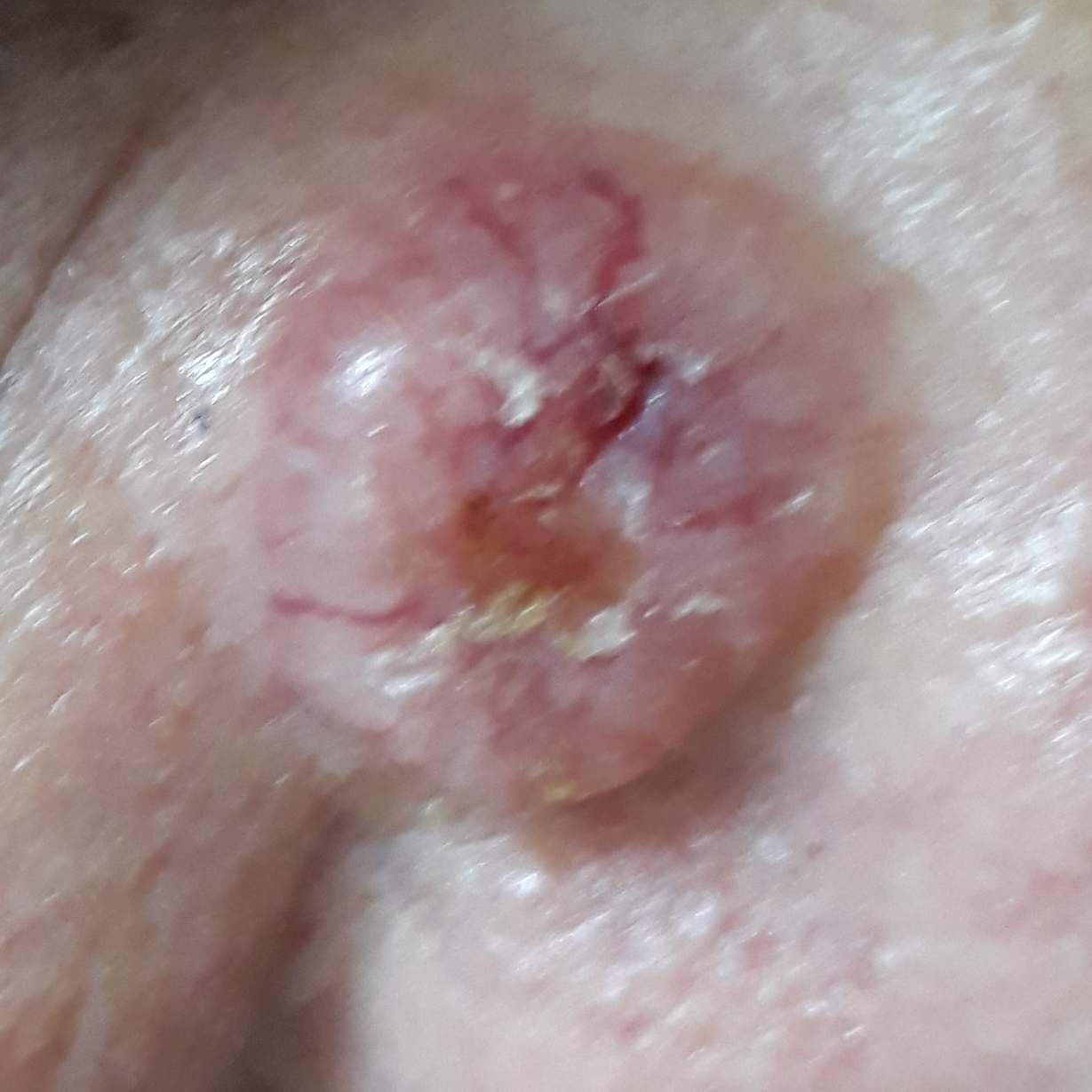| key | value |
|---|---|
| pathology | basal cell carcinoma (biopsy-proven) |